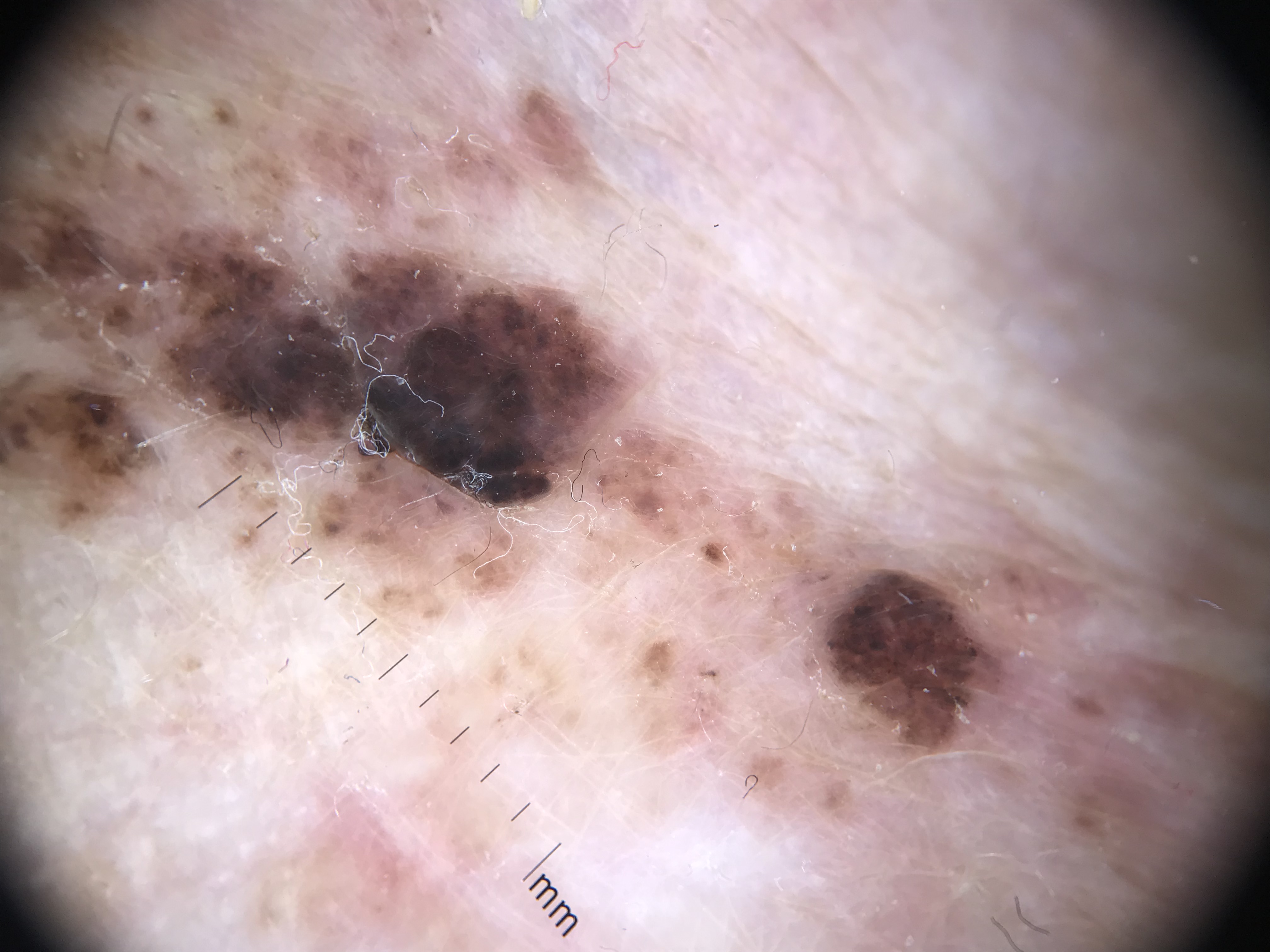Q: What is the diagnosis?
A: congenital compound nevus (expert consensus)